A dermatoscopic image of a skin lesion: 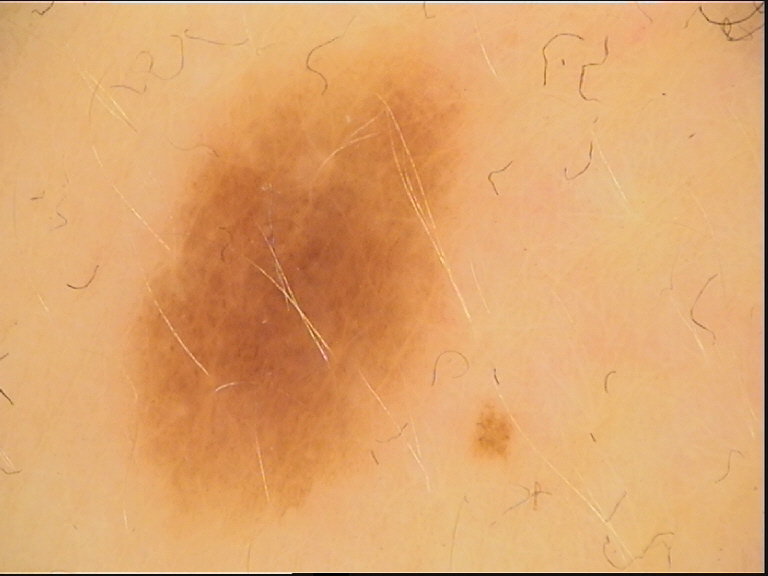Conclusion: Consistent with a benign lesion — a dysplastic junctional nevus.